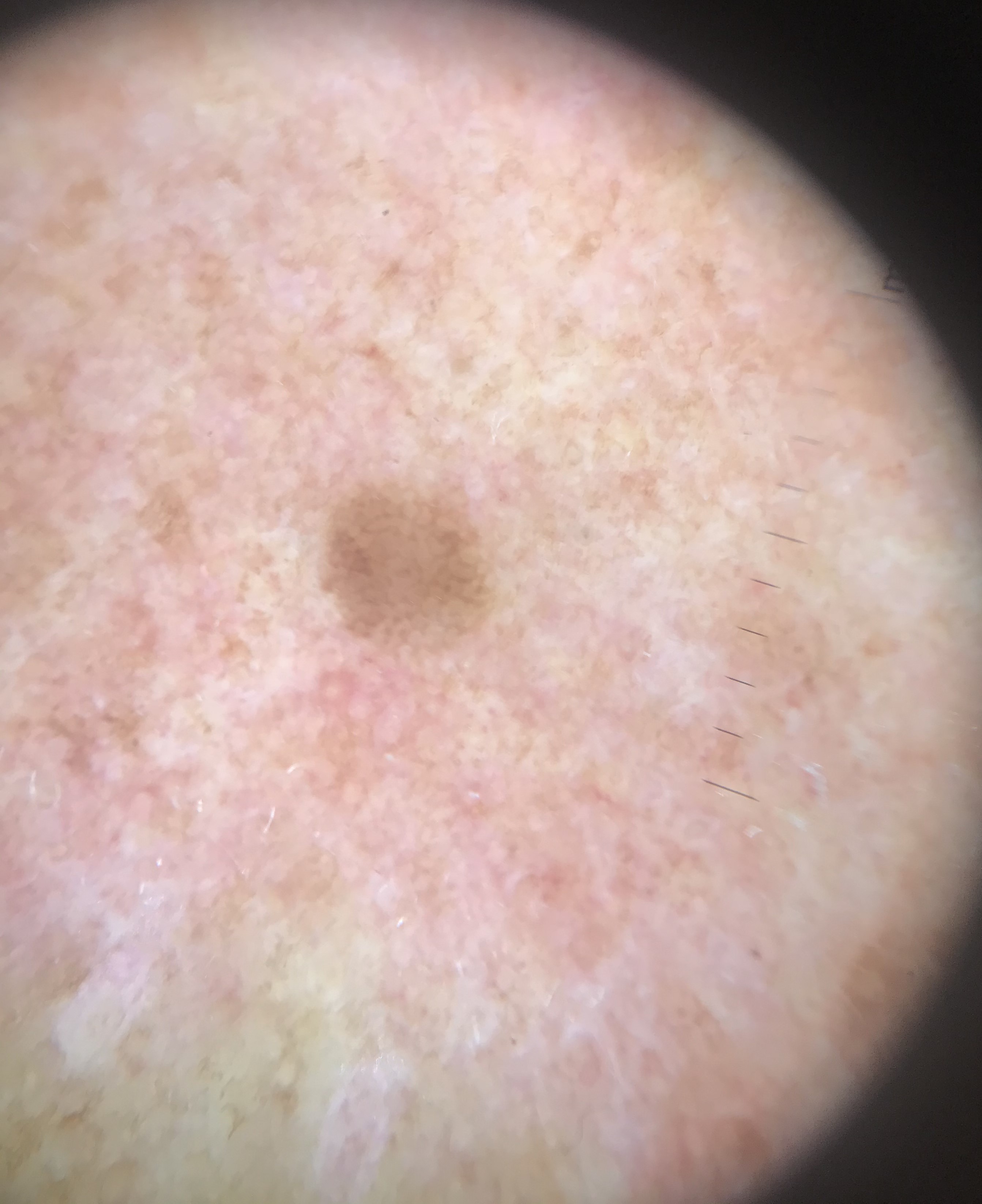Q: What is this lesion?
A: seborrheic keratosis (expert consensus)